A dermoscopic photograph of a skin lesion.
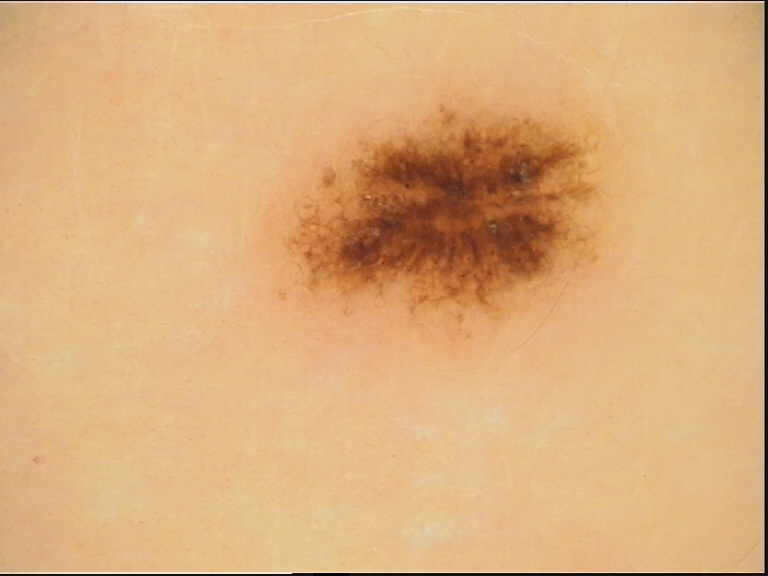diagnosis: dysplastic junctional nevus (expert consensus).